A dermoscopy image of a single skin lesion.
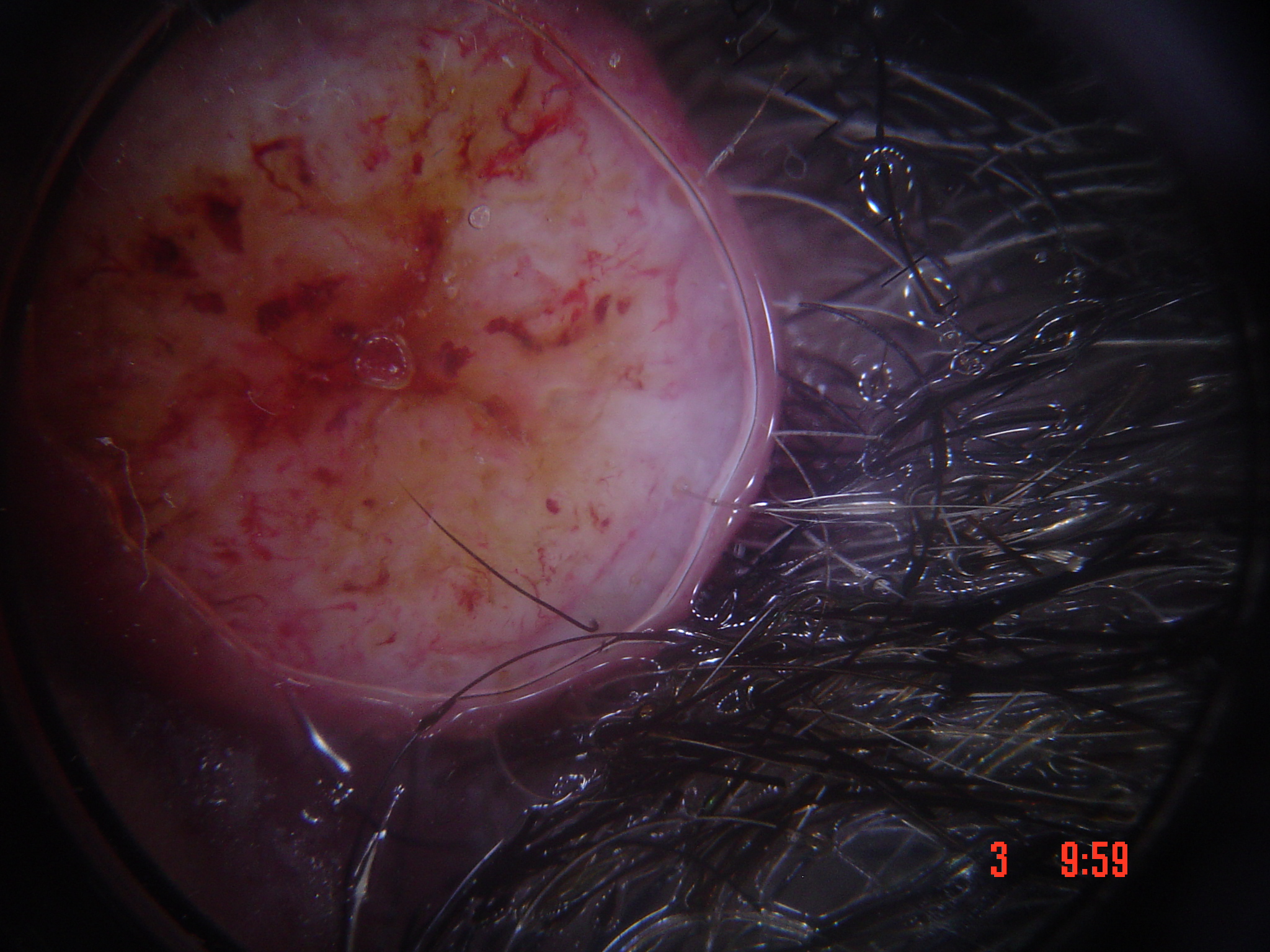Histopathologically confirmed as a keratinocytic lesion — a squamous cell carcinoma.